Acquired for a research image collection, with no referral diagnosis. The patient says their skin tans without first burning. A male subject 72 years old. The patient describes having a moderate number of moles. A dermoscopic image of a skin lesion:
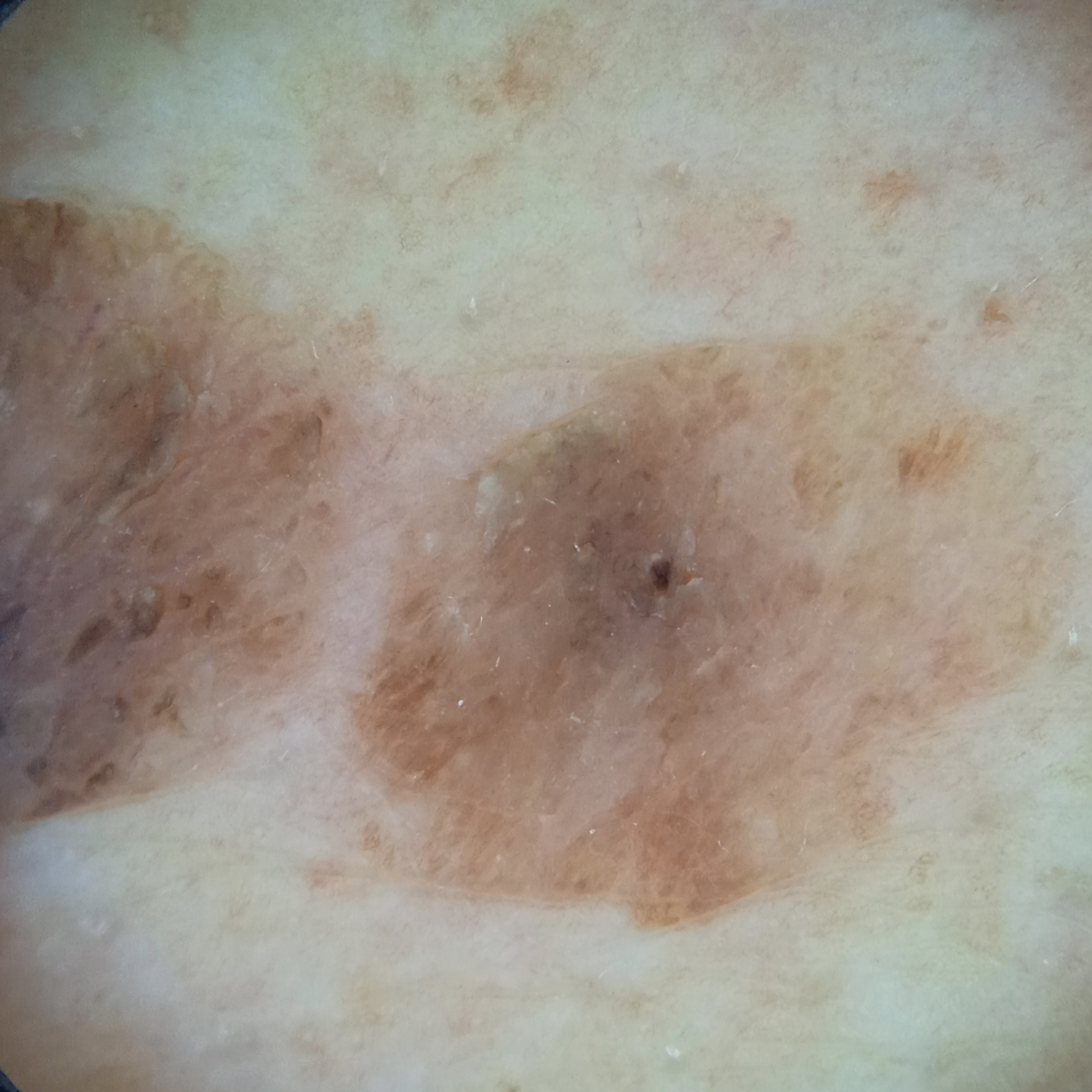The lesion is on the back.
Measuring roughly 12.8 mm.
Dermatologist review favored a seborrheic keratosis.